The patient reports the lesion is raised or bumpy · the photograph was taken at an angle · male patient, age 40–49 · no constitutional symptoms were reported · skin tone: Fitzpatrick II · self-categorized by the patient as a rash · present for one to three months · the arm is involved — 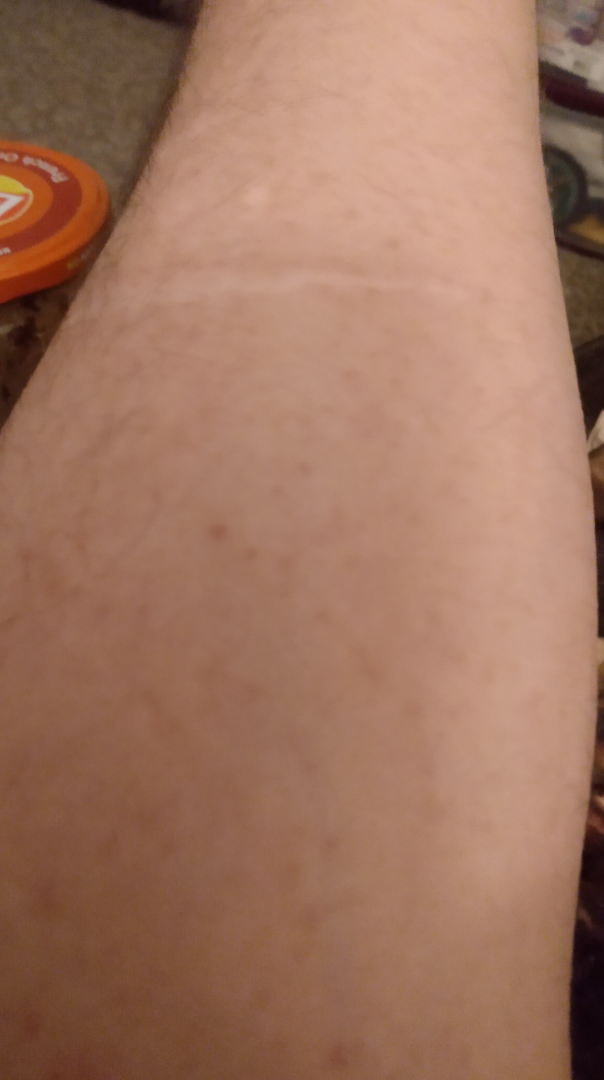The skin condition could not be confidently assessed from this image.